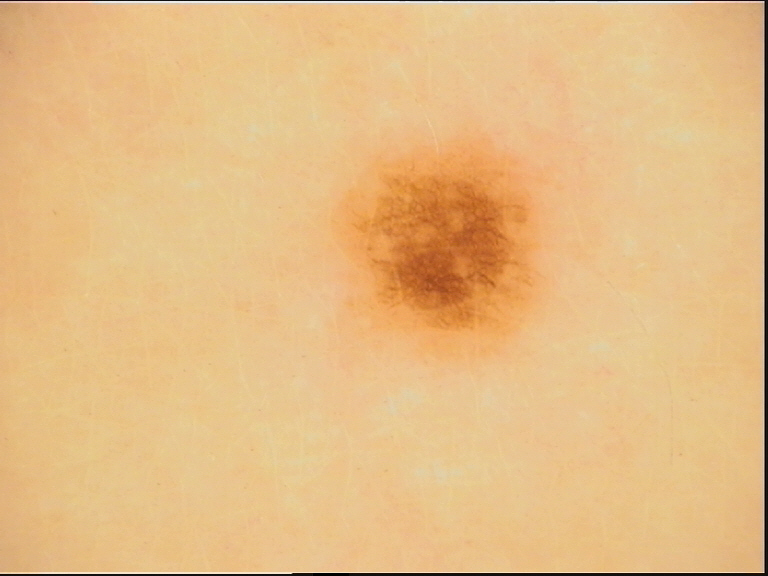A dermoscopy image of a single skin lesion.
The diagnosis was a benign lesion — a dysplastic junctional nevus.